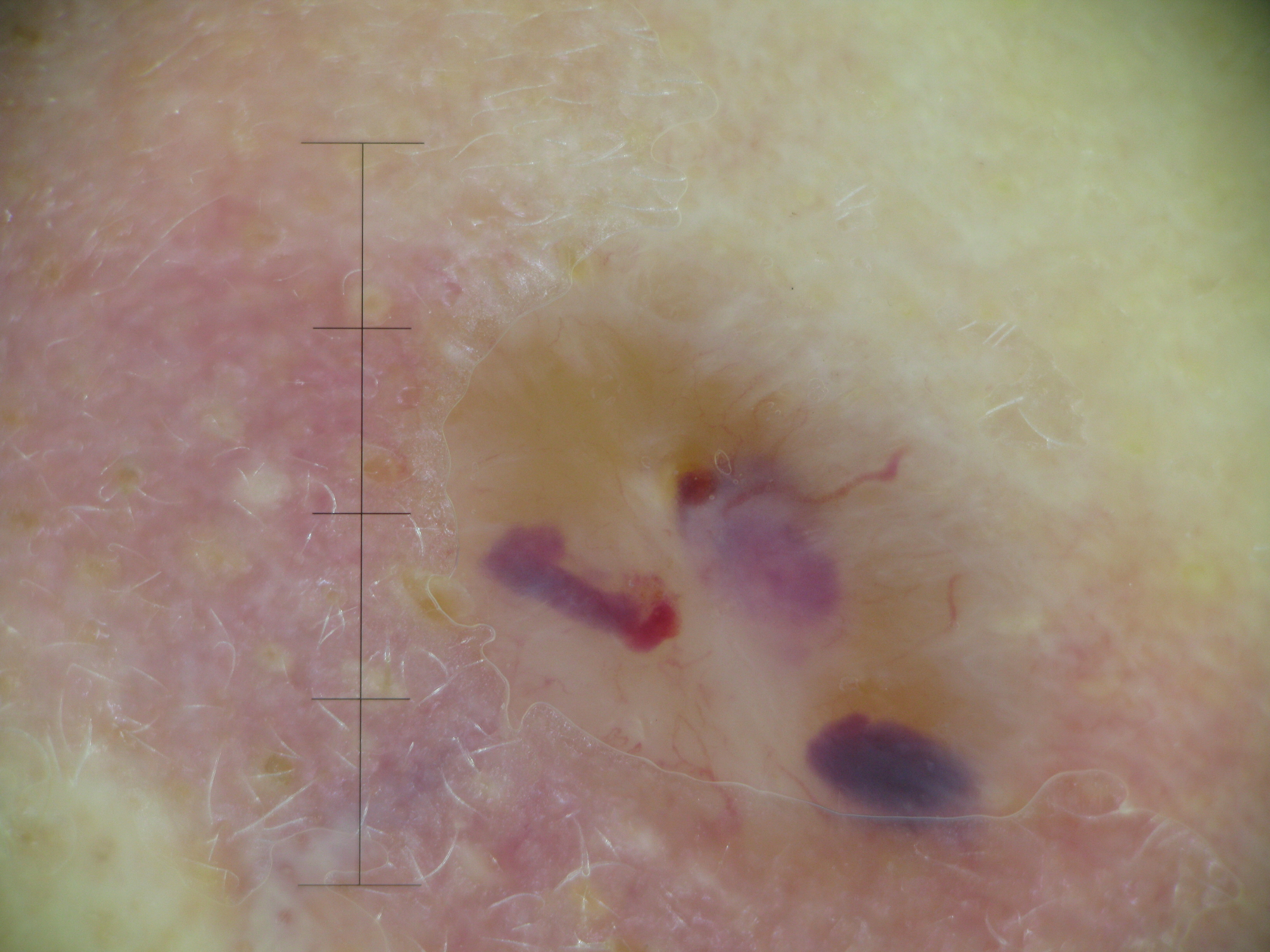{
  "image": "dermatoscopy",
  "lesion_type": {
    "main_class": "keratinocytic"
  },
  "diagnosis": {
    "name": "basal cell carcinoma",
    "code": "bcc",
    "malignancy": "malignant",
    "super_class": "non-melanocytic",
    "confirmation": "histopathology"
  }
}